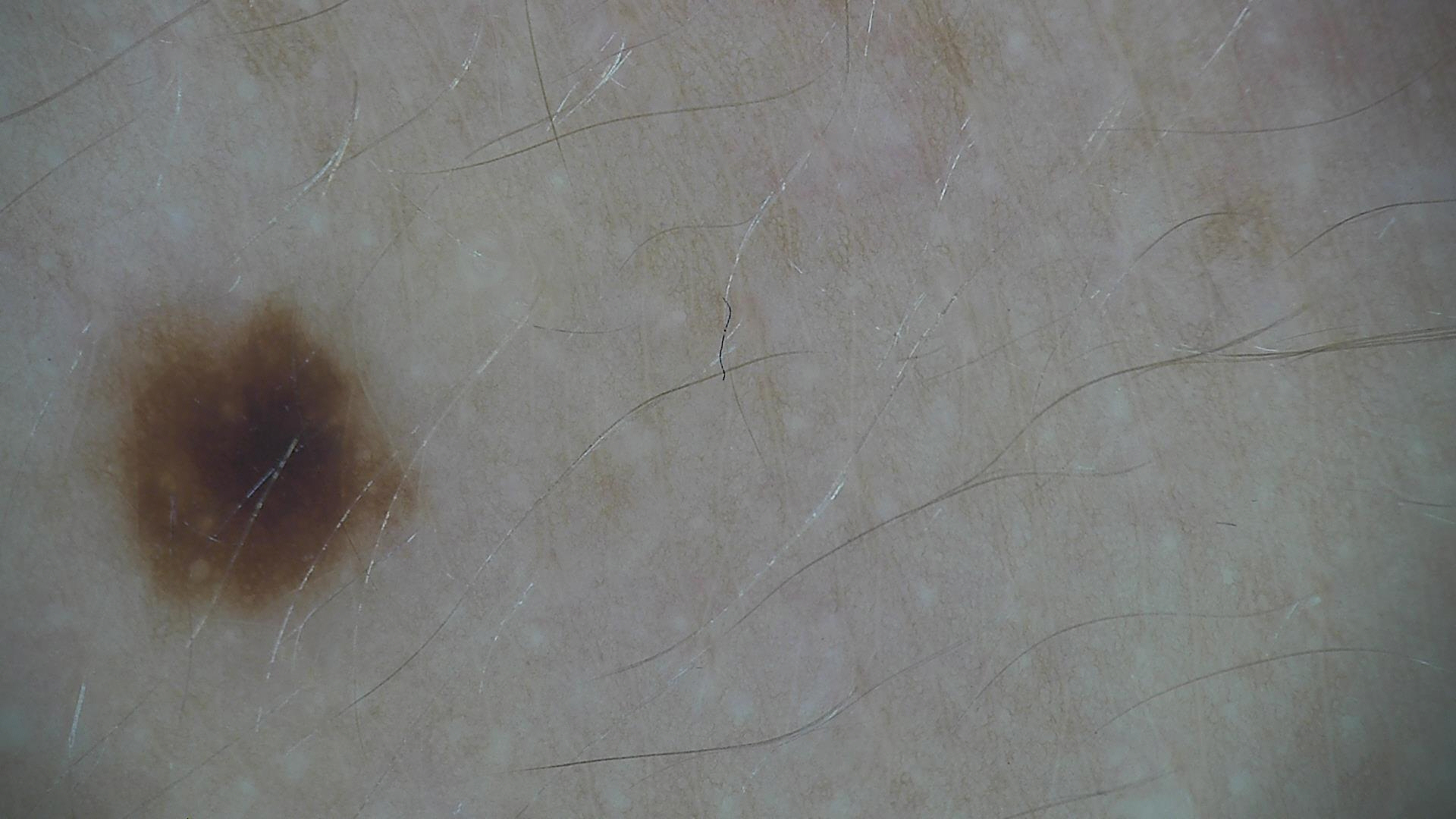A dermoscopic photograph of a skin lesion. The diagnosis was a dysplastic junctional nevus.